A dermoscopy image of a single skin lesion: 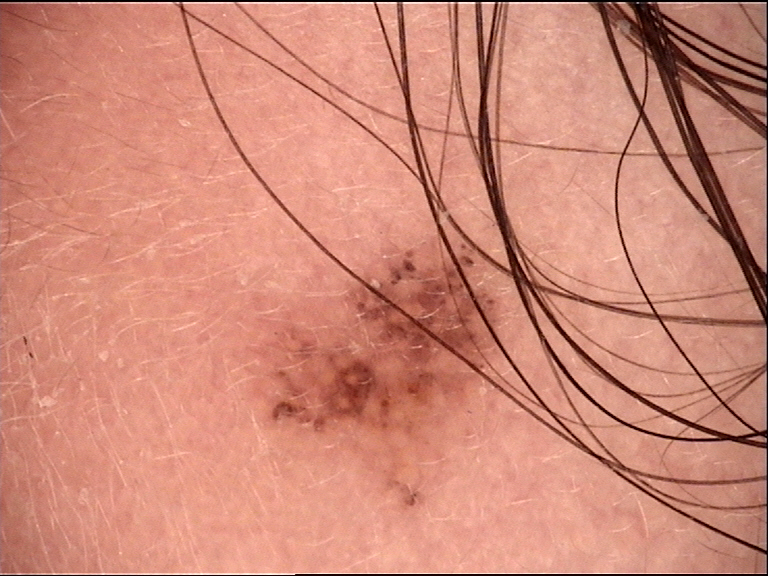Consistent with a benign lesion — a dysplastic junctional nevus.